A skin lesion imaged with a dermatoscope: 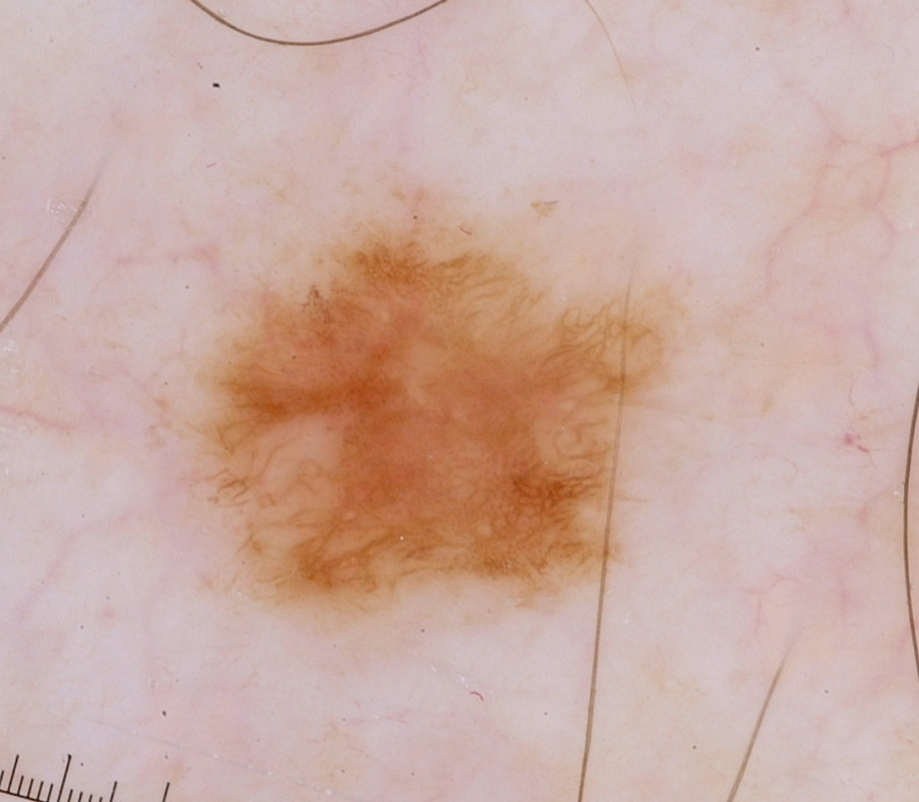Q: How much of the field does the lesion occupy?
A: ~26% of the field
Q: Where is the lesion in the image?
A: [154,167,706,637]
Q: What dermoscopic features are present?
A: pigment network and globules; absent: milia-like cysts, negative network, and streaks
Q: What did the assessment conclude?
A: a melanoma